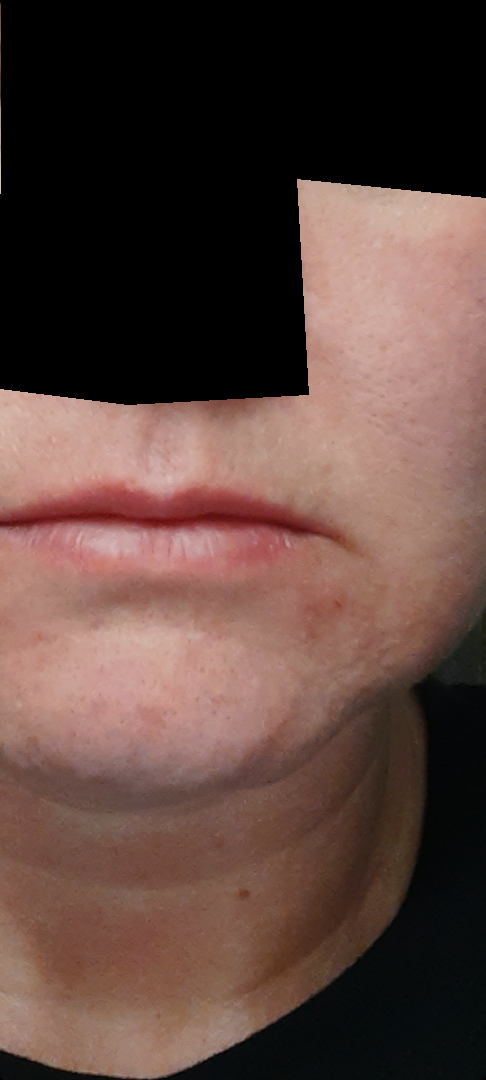{
  "differential": {
    "leading": [
      "Perioral Dermatitis"
    ],
    "considered": [
      "Irritant Contact Dermatitis"
    ],
    "unlikely": [
      "Perleche",
      "Seborrheic Dermatitis",
      "Acne"
    ]
  }
}